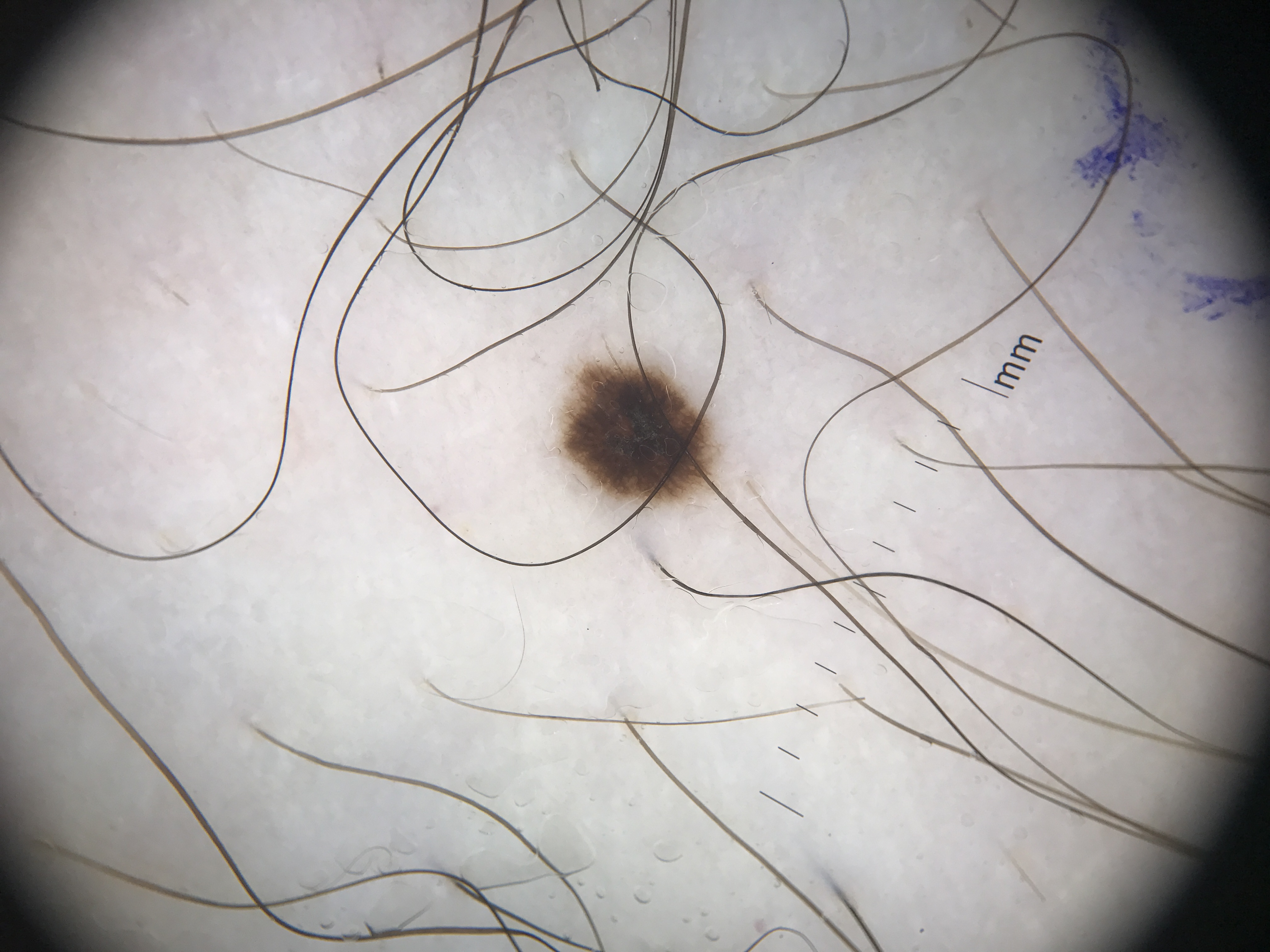Labeled as a dysplastic junctional nevus.